A dermatoscopic image of a skin lesion:
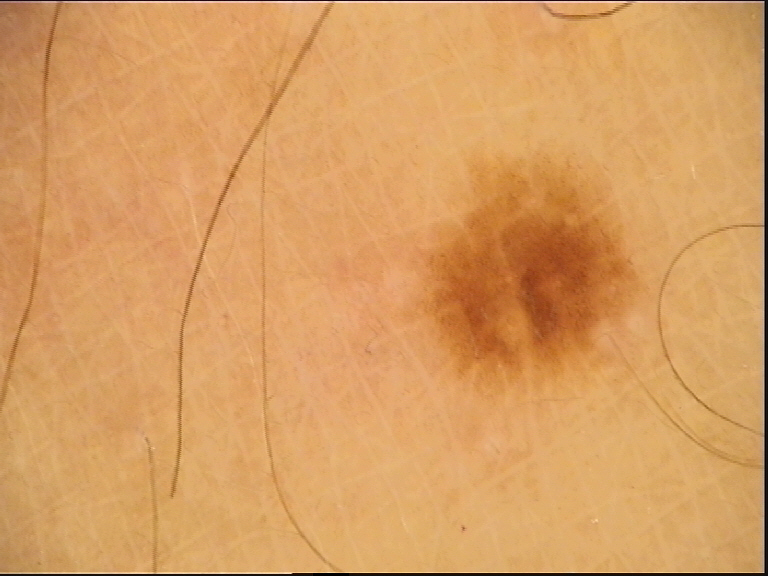The diagnosis was a dysplastic junctional nevus.